A dermoscopic image of a skin lesion.
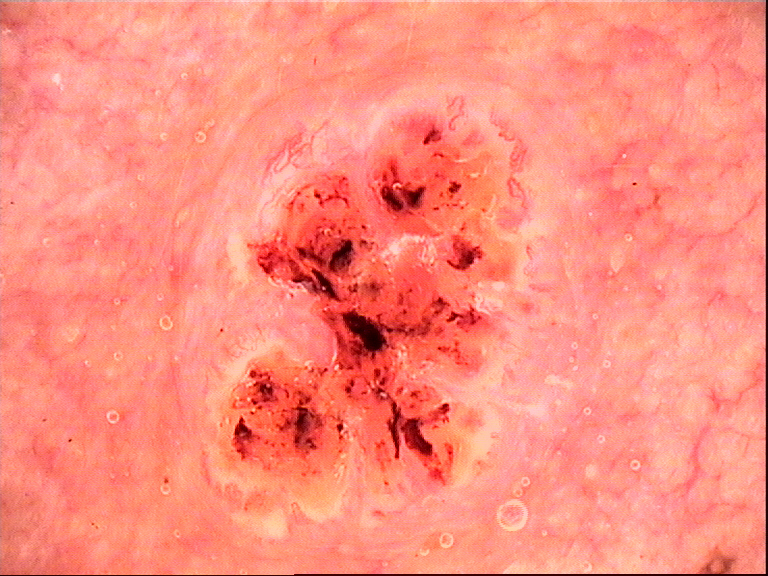Q: What kind of lesion is this?
A: keratinocytic
Q: What did the workup show?
A: squamous cell carcinoma (biopsy-proven)